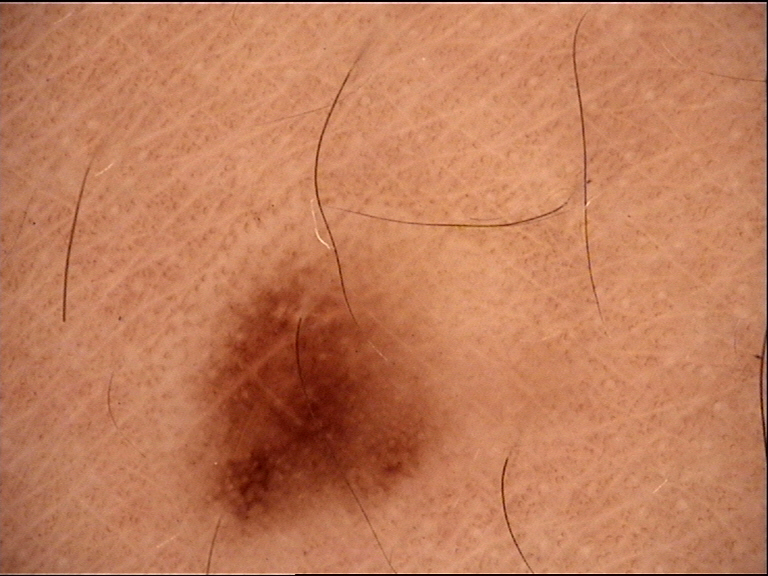Impression:
Labeled as a dysplastic junctional nevus.